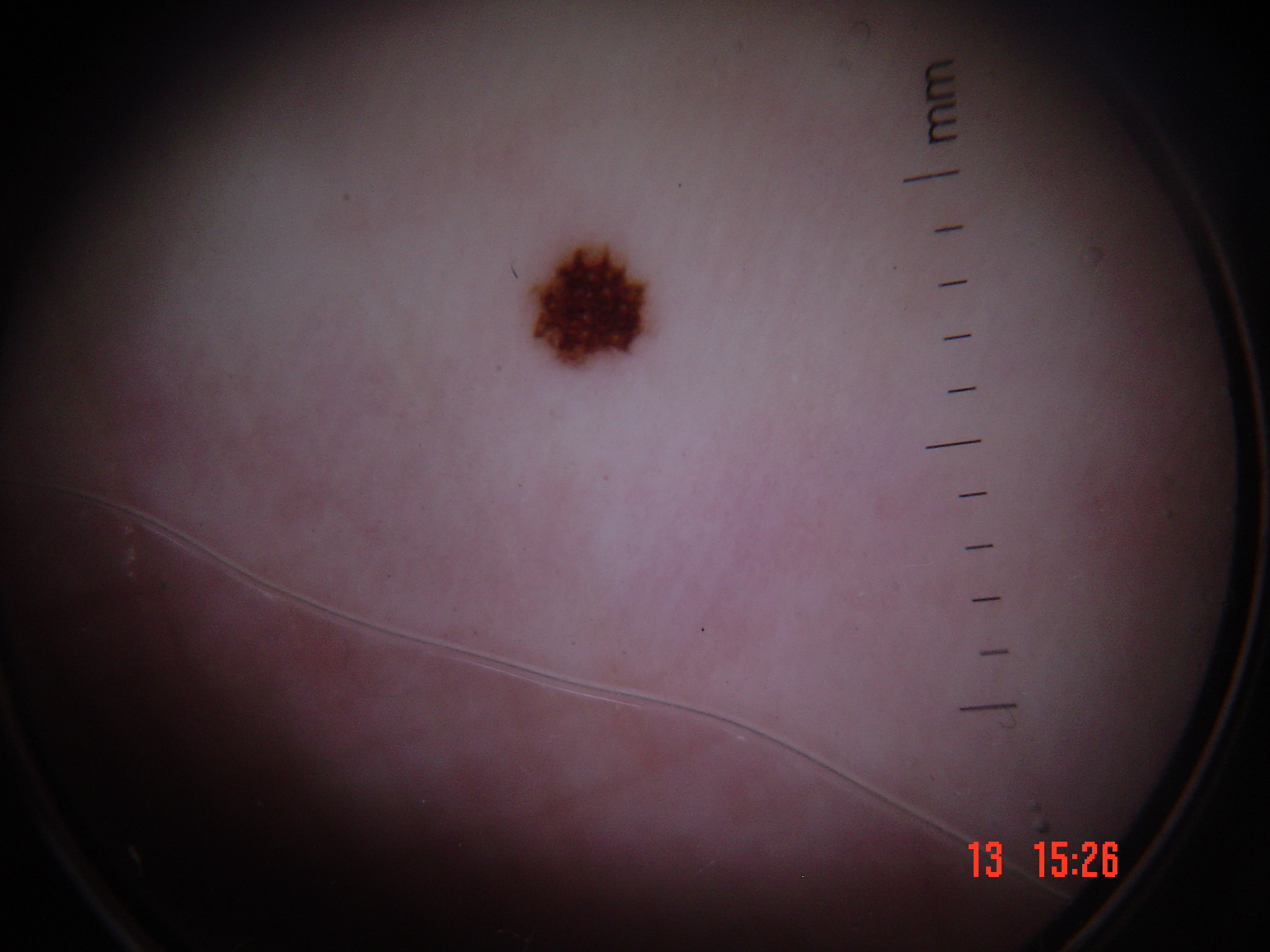A skin lesion imaged with a dermatoscope.
The diagnostic label was an acral dysplastic junctional nevus.